An image taken at an angle, the lesion involves the top or side of the foot and leg — 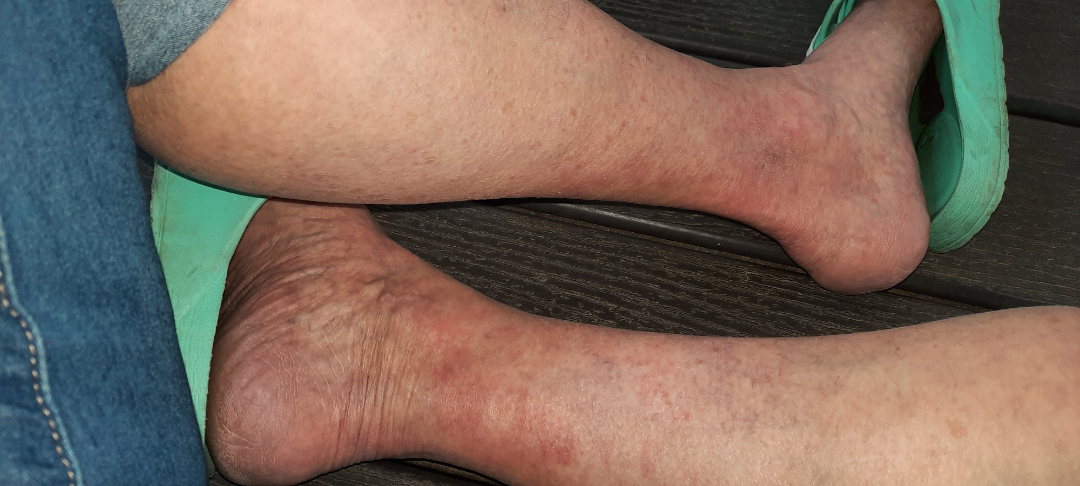assessment: not assessable | self-categorized as: skin that appeared healthy to them | present for: more than one year | patient-reported symptoms: enlargement, pain, itching and bothersome appearance.